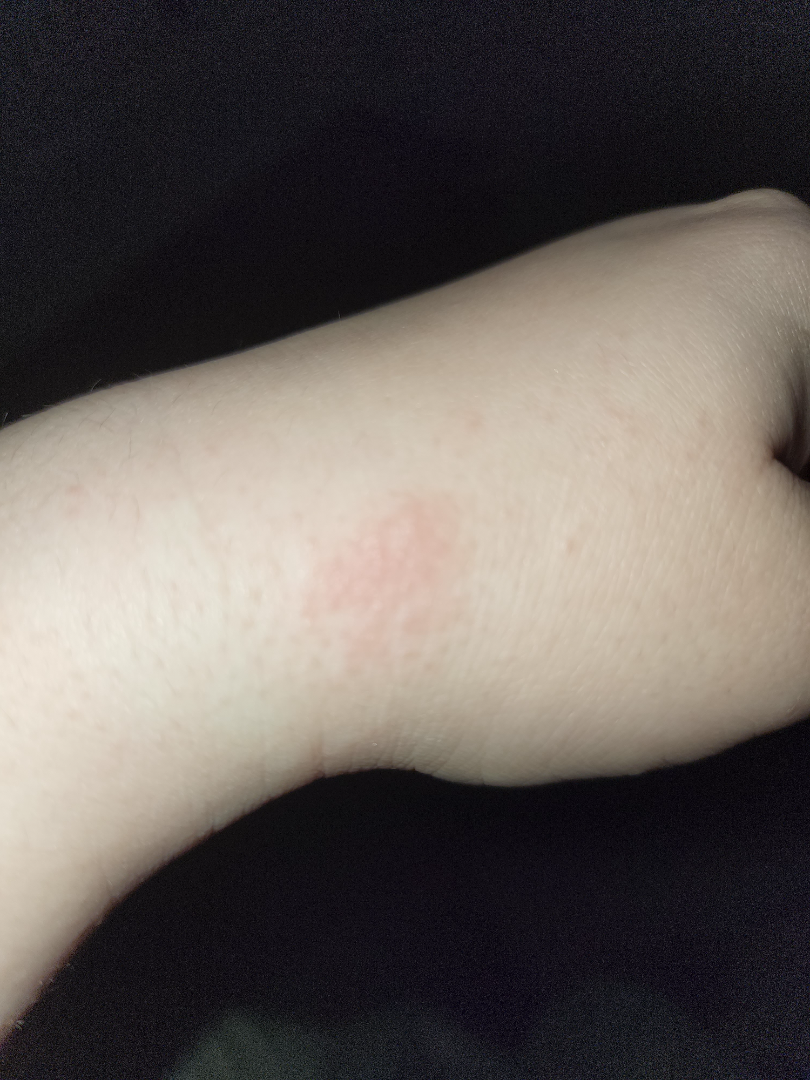The patient indicates itching.
Self-categorized by the patient as a rash.
Skin tone: FST I; human graders estimated Monk Skin Tone 3 (US pool) or 1 (India pool).
The condition has been present for less than one week.
The patient indicates the lesion is raised or bumpy.
The photograph is a close-up of the affected area.
The back of the hand is involved.
One reviewing dermatologist: the differential, in no particular order, includes Eczema and Allergic Contact Dermatitis.